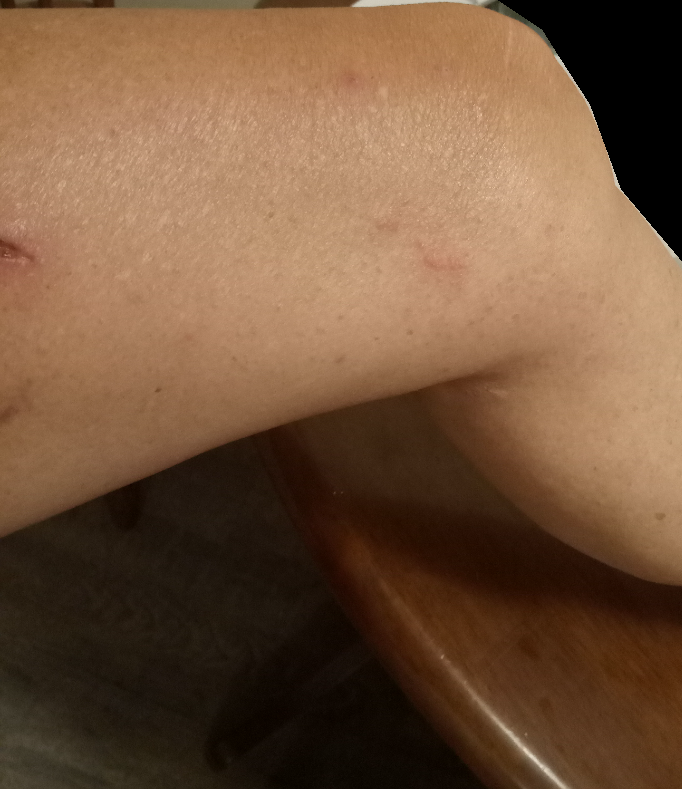The affected area is the leg. This image was taken at a distance. The patient also reports chills. The contributor is a female aged 50–59. The condition has been present for about one day. The patient notes burning, enlargement and bothersome appearance. On remote dermatologist review: the differential, in no particular order, includes Insect Bite and Allergic Contact Dermatitis; an alternative is Herpes Zoster.